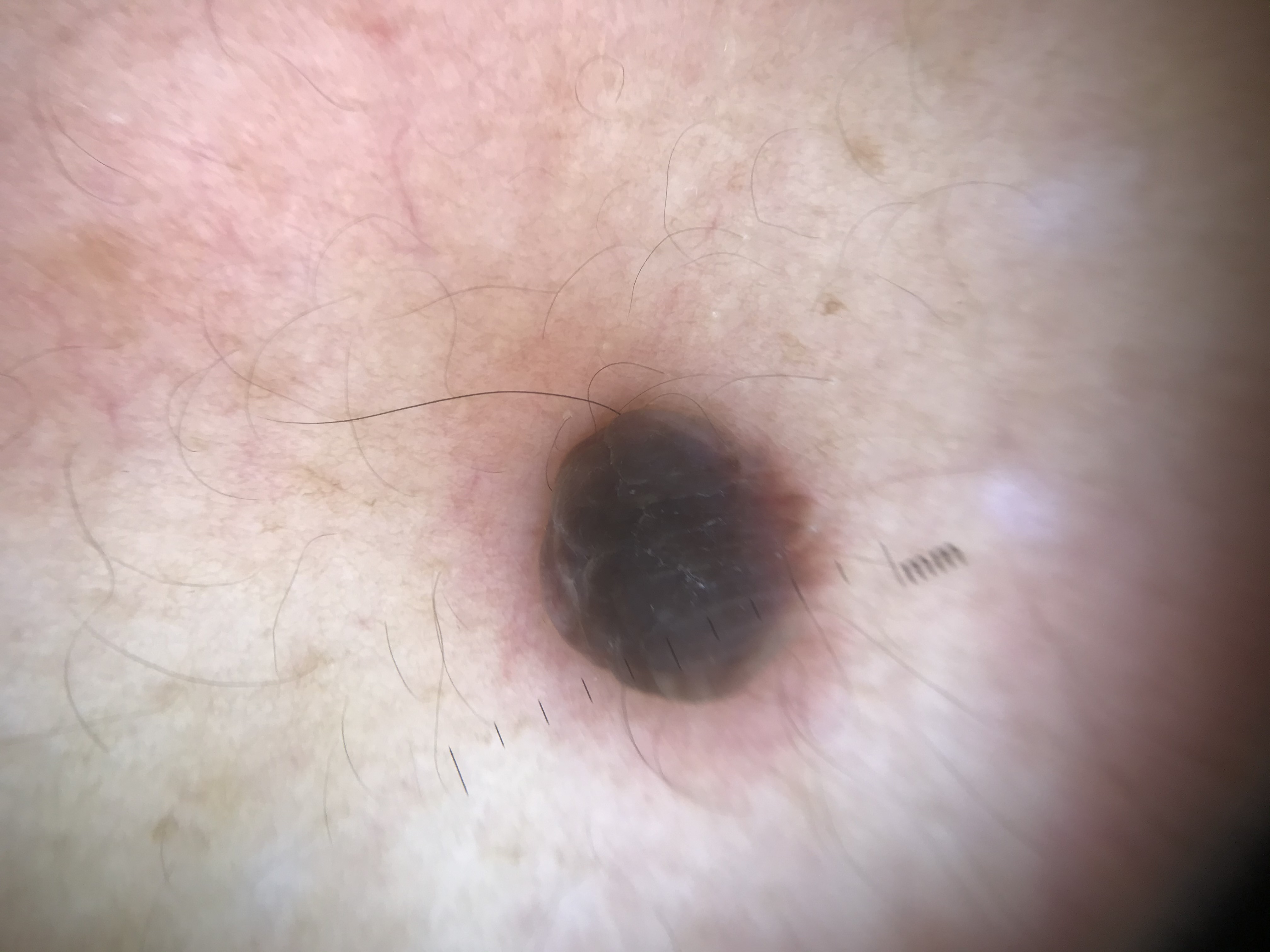Conclusion: The diagnostic label was a banal lesion — a dermal nevus.